A female patient approximately 40 years of age, a dermatoscopic image of a skin lesion:
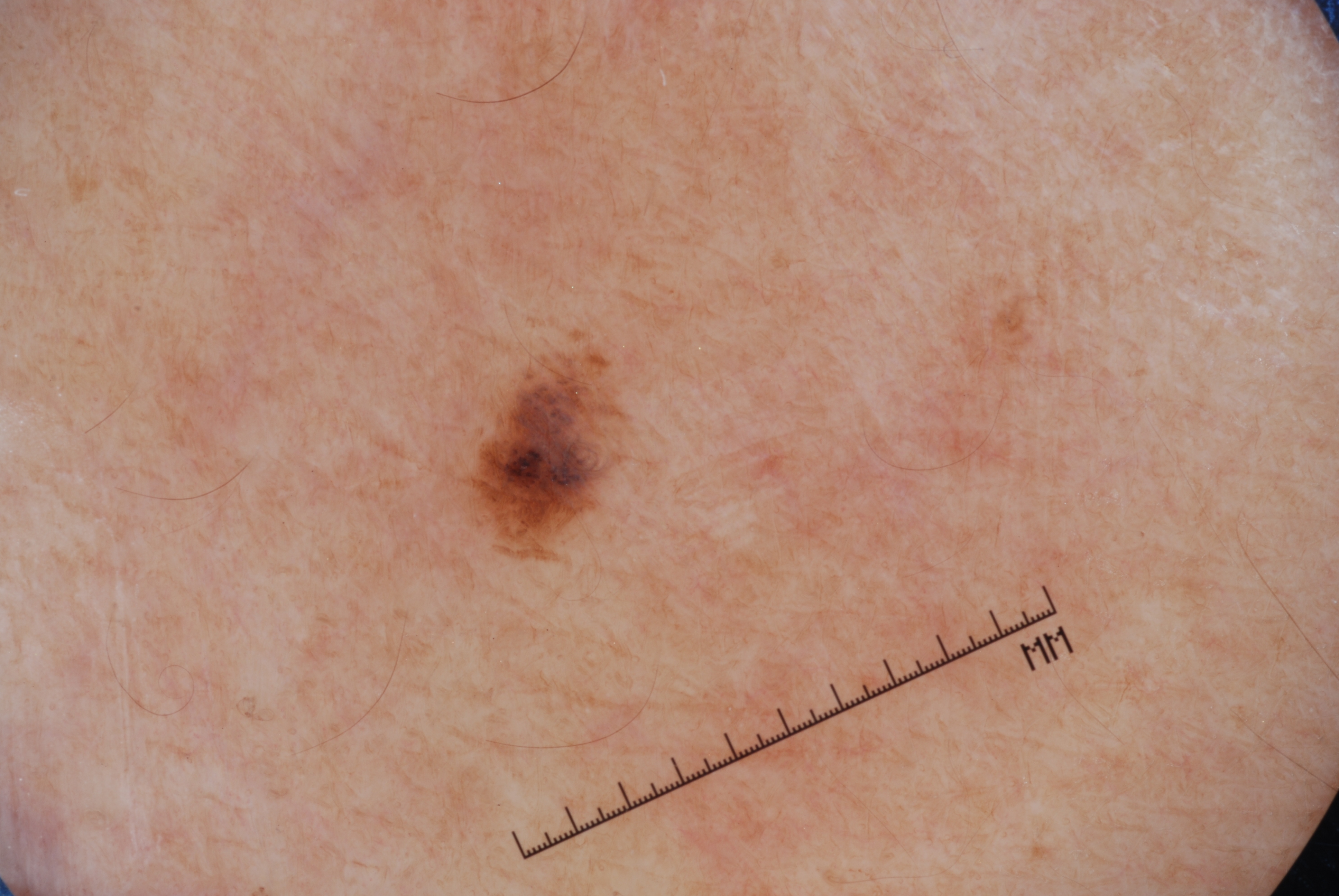Summary:
Dermoscopic examination shows no pigment network, negative network, milia-like cysts, or streaks. The visible lesion spans x1=439, y1=342, x2=631, y2=561.
Conclusion:
Diagnosed as a melanocytic nevus.